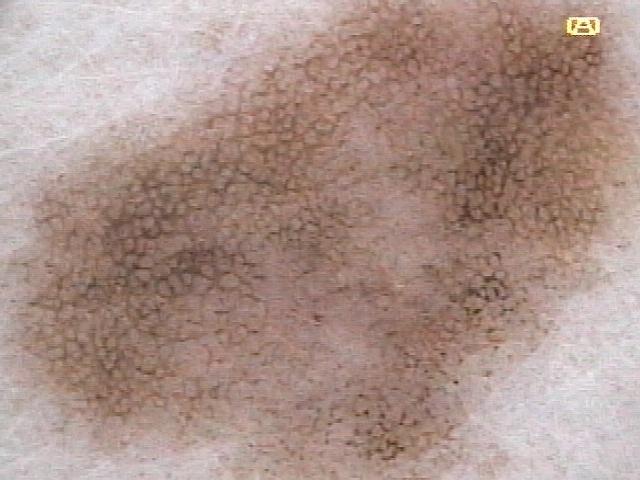A female patient in their mid-50s.
Dermoscopy of a skin lesion.
Located on the trunk.
Clinically diagnosed as a lesion of melanocytic lineage — a nevus.